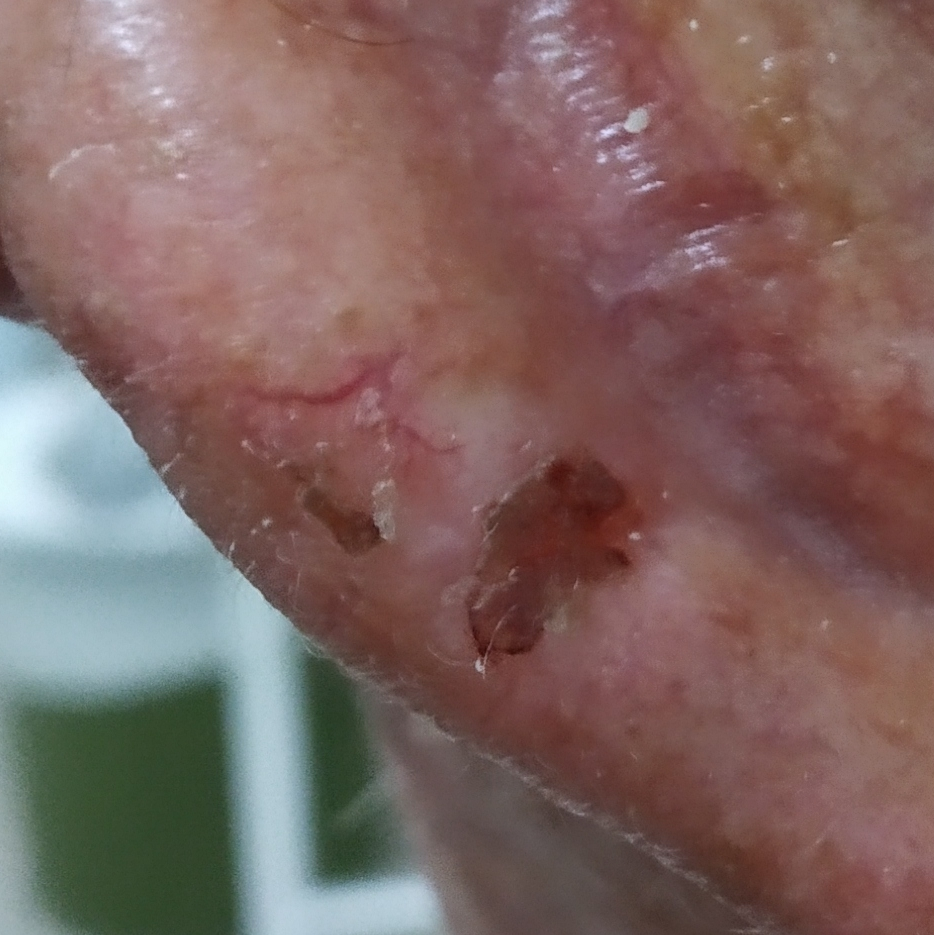image: clinical photograph
patient:
  age: 78
  gender: male
lesion_location: an ear
symptoms:
  present:
    - pain
    - itching
    - elevation
    - bleeding
diagnosis:
  name: basal cell carcinoma
  code: BCC
  malignancy: malignant
  confirmation: histopathology